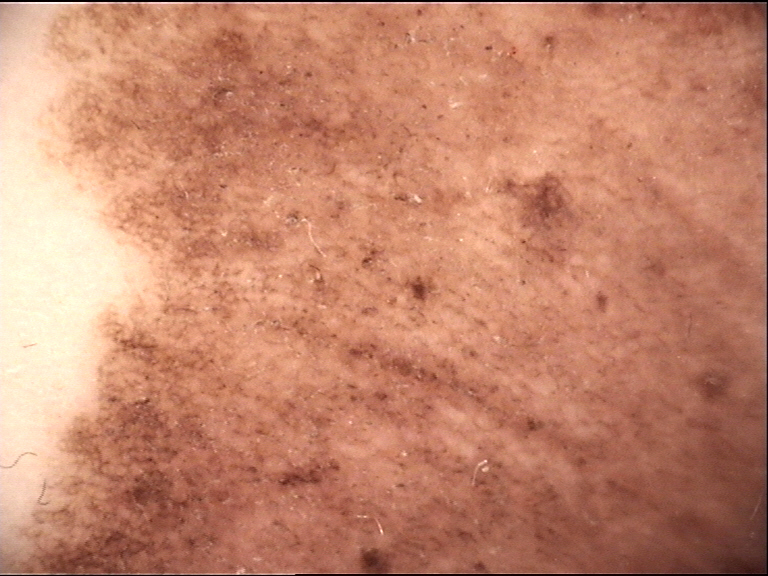Q: What is this lesion?
A: congenital compound nevus (expert consensus)